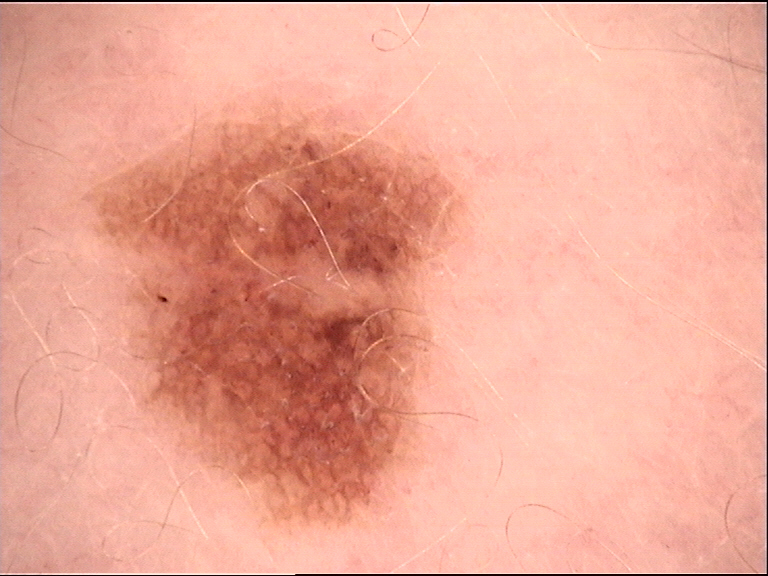<dermoscopy>
  <diagnosis>
    <name>dysplastic junctional nevus</name>
    <code>jd</code>
    <malignancy>benign</malignancy>
    <super_class>melanocytic</super_class>
    <confirmation>expert consensus</confirmation>
  </diagnosis>
</dermoscopy>